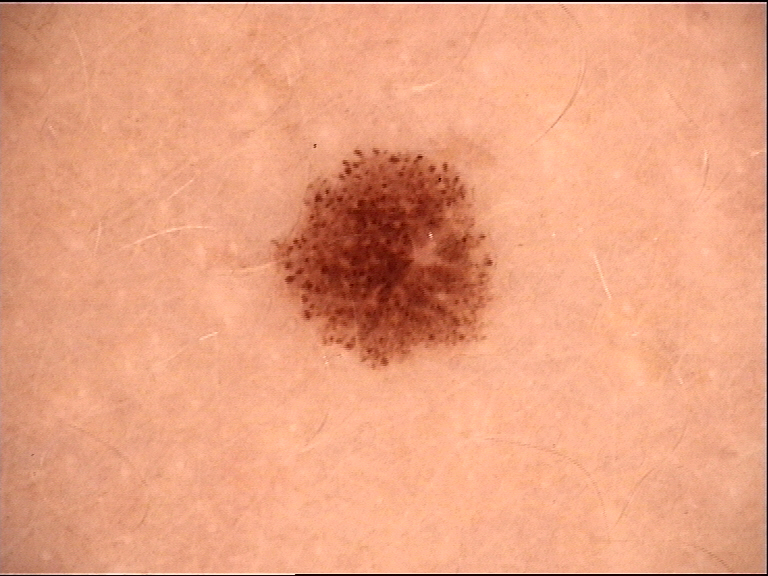Dermoscopy of a skin lesion.
Classified as a dysplastic junctional nevus.